The subject is male. Close-up view. The lesion involves the leg.
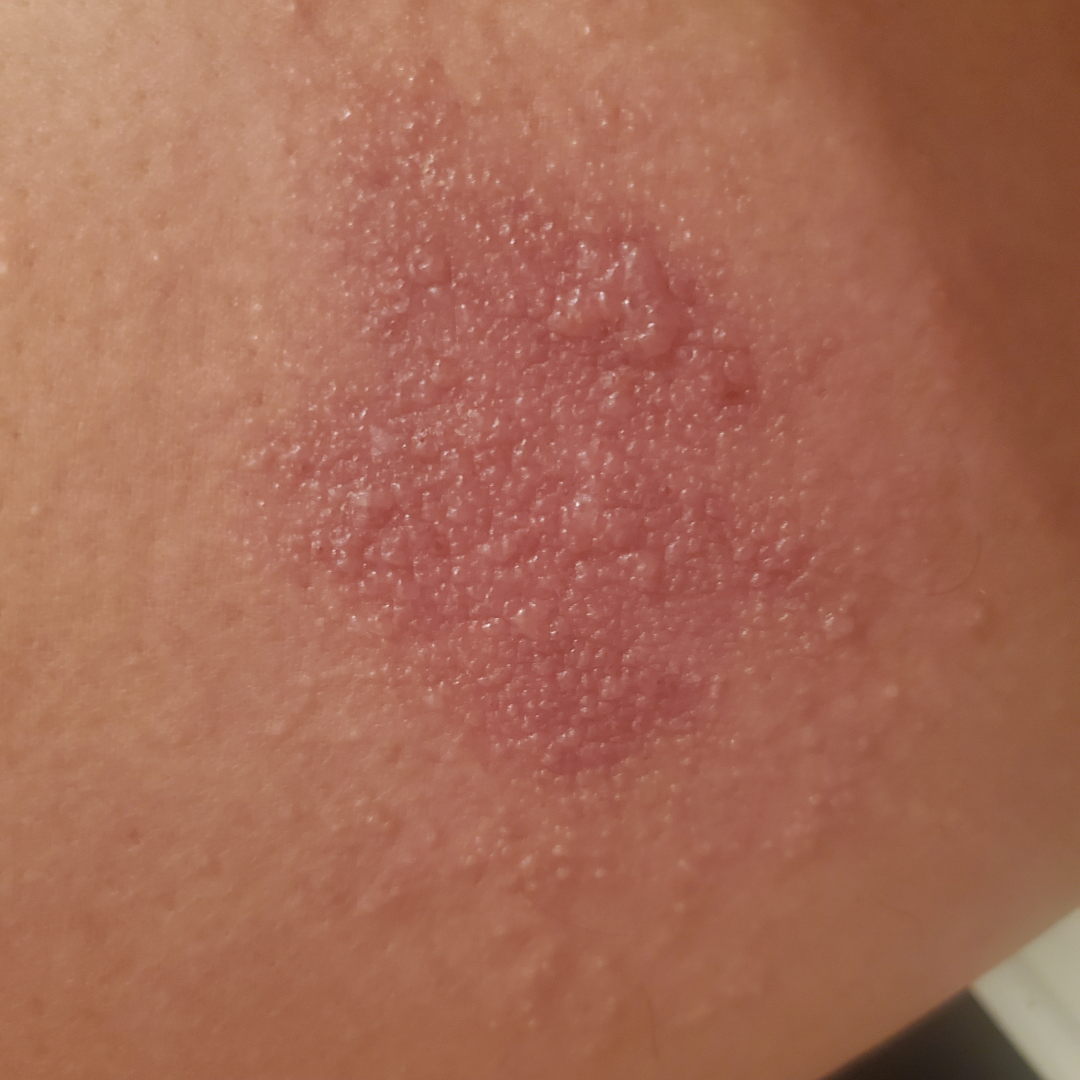symptoms:
  - enlargement
  - itching
systemic_symptoms: none reported
patient_category: a rash
duration: less than one week
texture: raised or bumpy
differential:
  leading:
    - Allergic Contact Dermatitis
  unlikely:
    - Herpes Simplex
    - Eczema
    - Impetigo
    - Herpes Zoster